The patient is a female aged 60–69, the sole of the foot and palm are involved, the photo was captured at a distance: 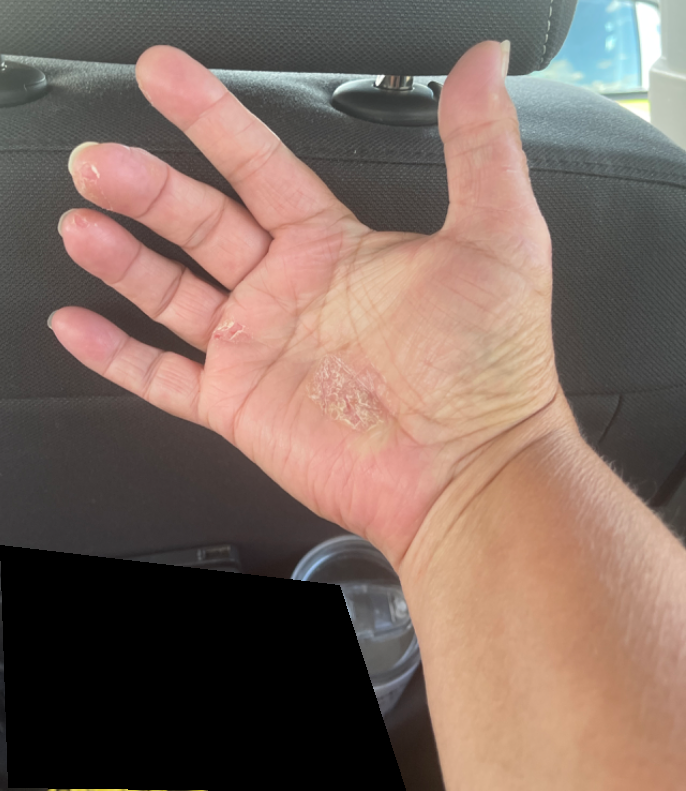constitutional symptoms = none reported | reported symptoms = enlargement, bothersome appearance, bleeding and itching | history = more than one year | patient's own categorization = a rash | texture = rough or flaky | assessment = three independent reviewers: the leading consideration is Psoriasis; also consider Eczema; lower on the differential is Tinea.